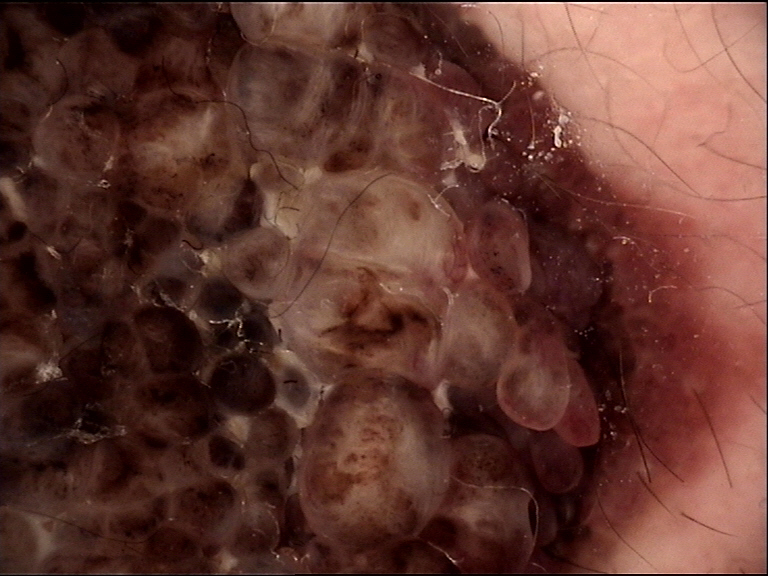Case:
A dermoscopic close-up of a skin lesion. This is a banal lesion.
Impression:
Classified as a congenital compound nevus.